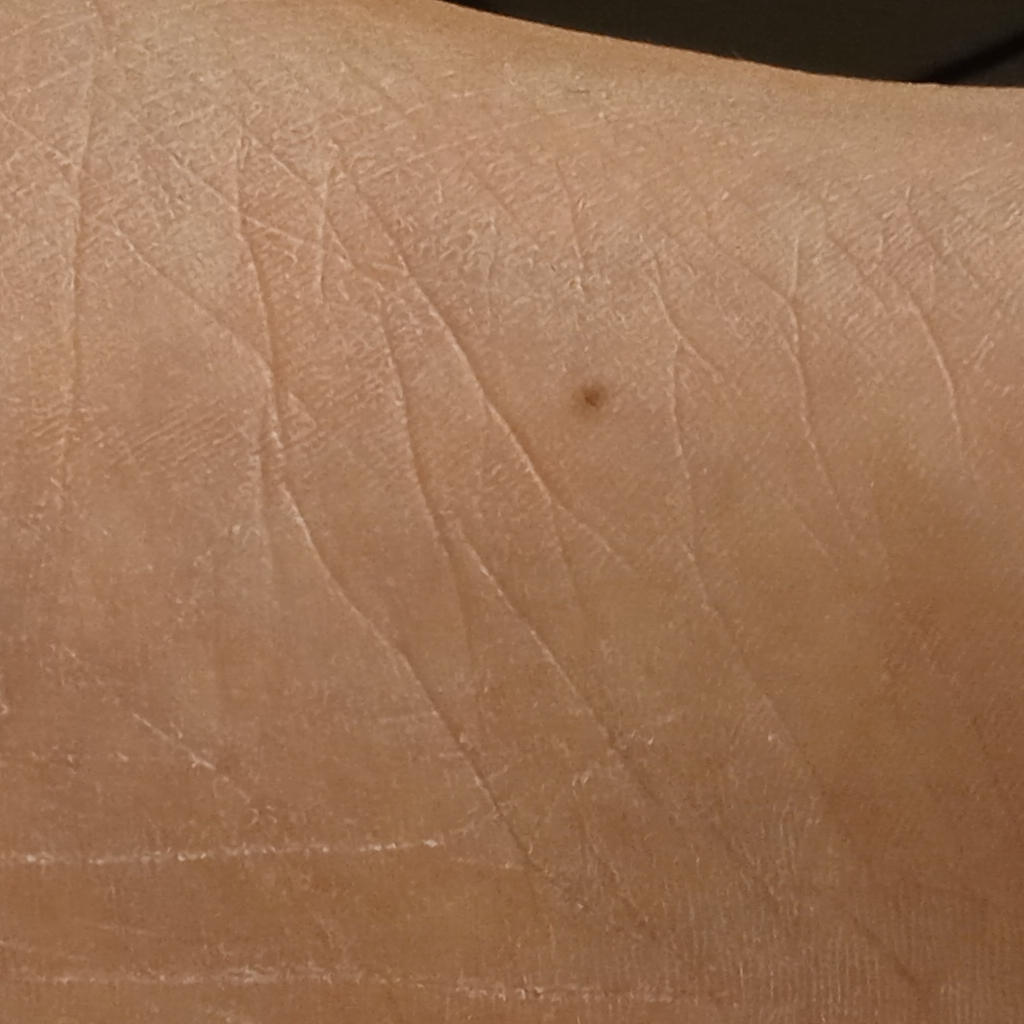The patient says their skin tans without first burning.
A macroscopic clinical photograph of a skin lesion.
On a questionnaire the patient reported a personal history of cancer.
The lesion measures approximately 2.2 mm.
The consensus diagnosis for this lesion was a melanocytic nevus.